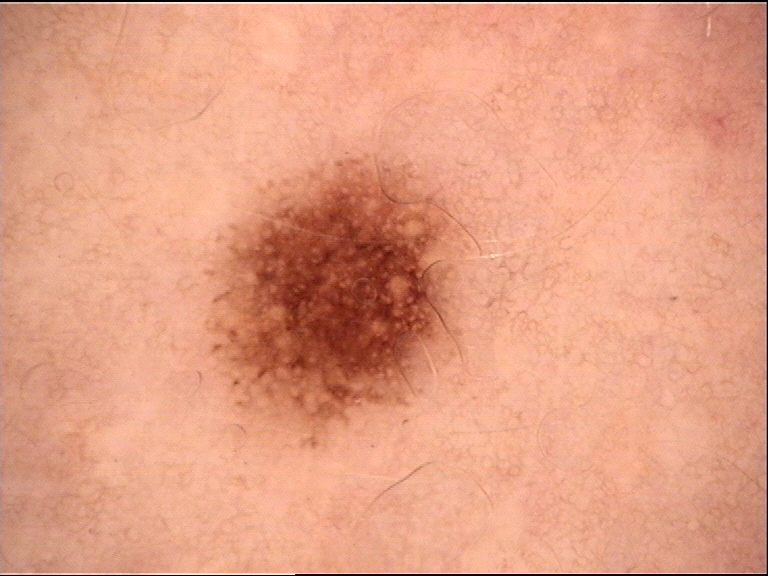Case:
Dermoscopy of a skin lesion.
Conclusion:
Labeled as a benign lesion — a dysplastic junctional nevus.